Close-up view, the subject is female, the affected area is the leg — 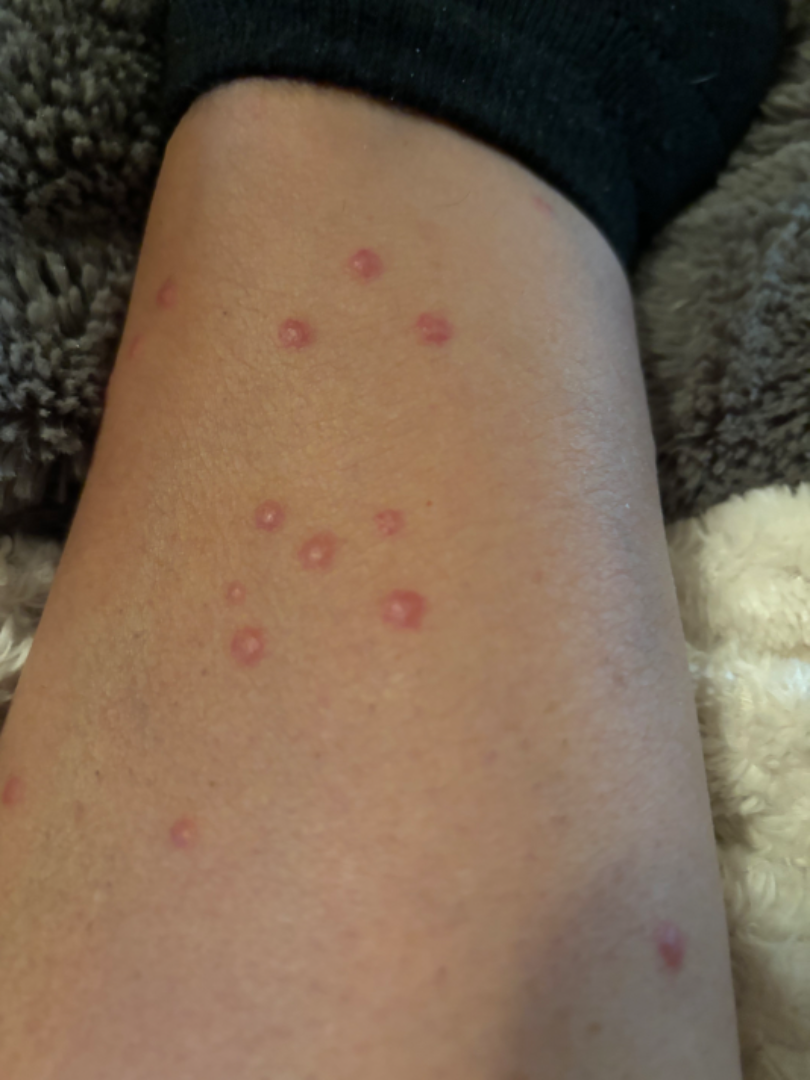Eruptive xanthoma (0.55); Cutaneous sarcoidosis (0.27); Primary cutaneous lymphoma (0.18).